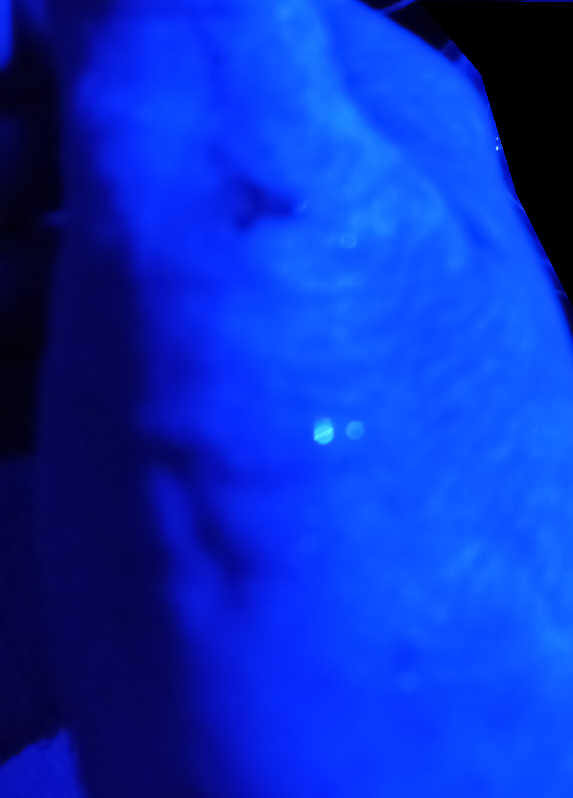{"assessment": "indeterminate from the photograph", "body_site": "palm", "systemic_symptoms": "none reported", "duration": "one to four weeks", "shot_type": "close-up", "texture": "fluid-filled", "symptoms": "itching"}